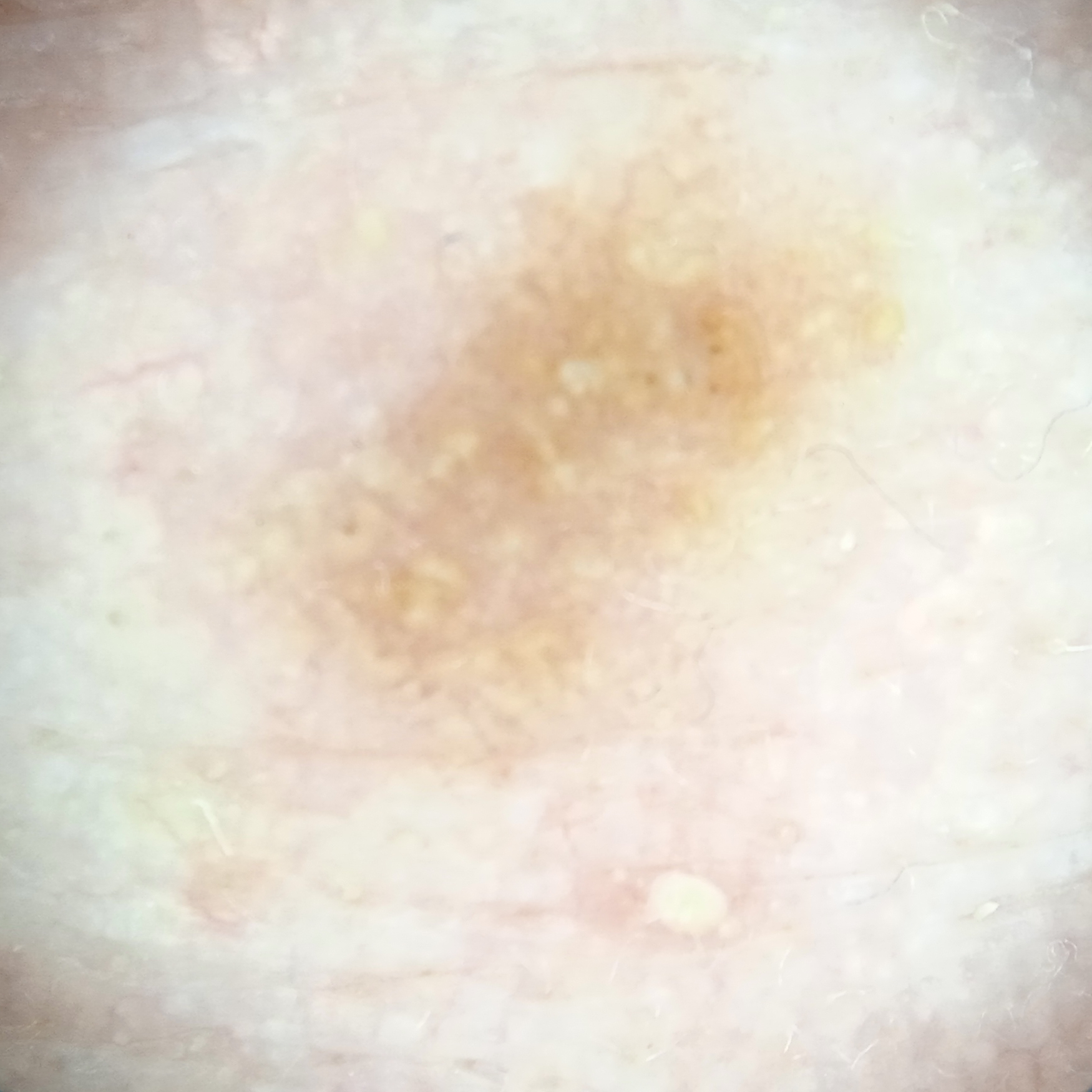image type: dermoscopy
sun reaction: skin reddens painfully with sun exposure
body site: the face
lesion size: 6.4 mm
diagnostic label: actinic keratosis (dermatologist consensus)